A male patient, approximately 60 years of age; a dermatoscopic image of a skin lesion:
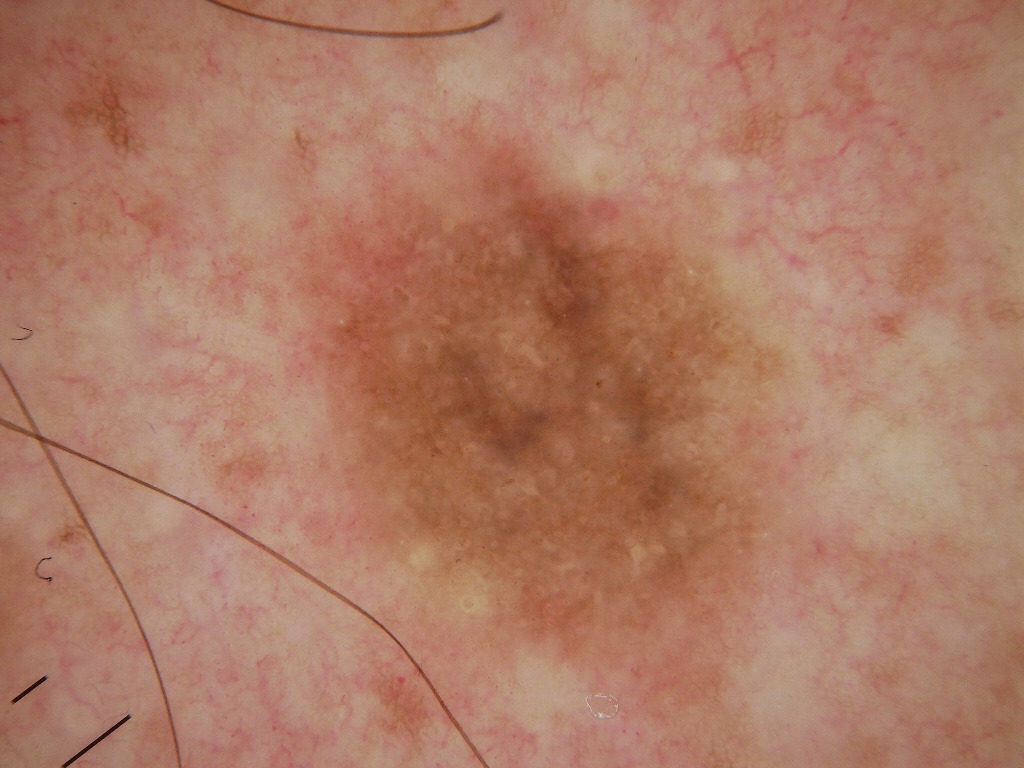Dermoscopic assessment notes milia-like cysts and negative network; no pigment network, globules, or streaks. The lesion spans x1=289, y1=152, x2=821, y2=747. The lesion takes up a large portion of the image. Consistent with a melanocytic nevus, a benign skin lesion.